Acquired for a research image collection, with no referral diagnosis; a dermoscopy image of a skin lesion; a female patient aged 72: 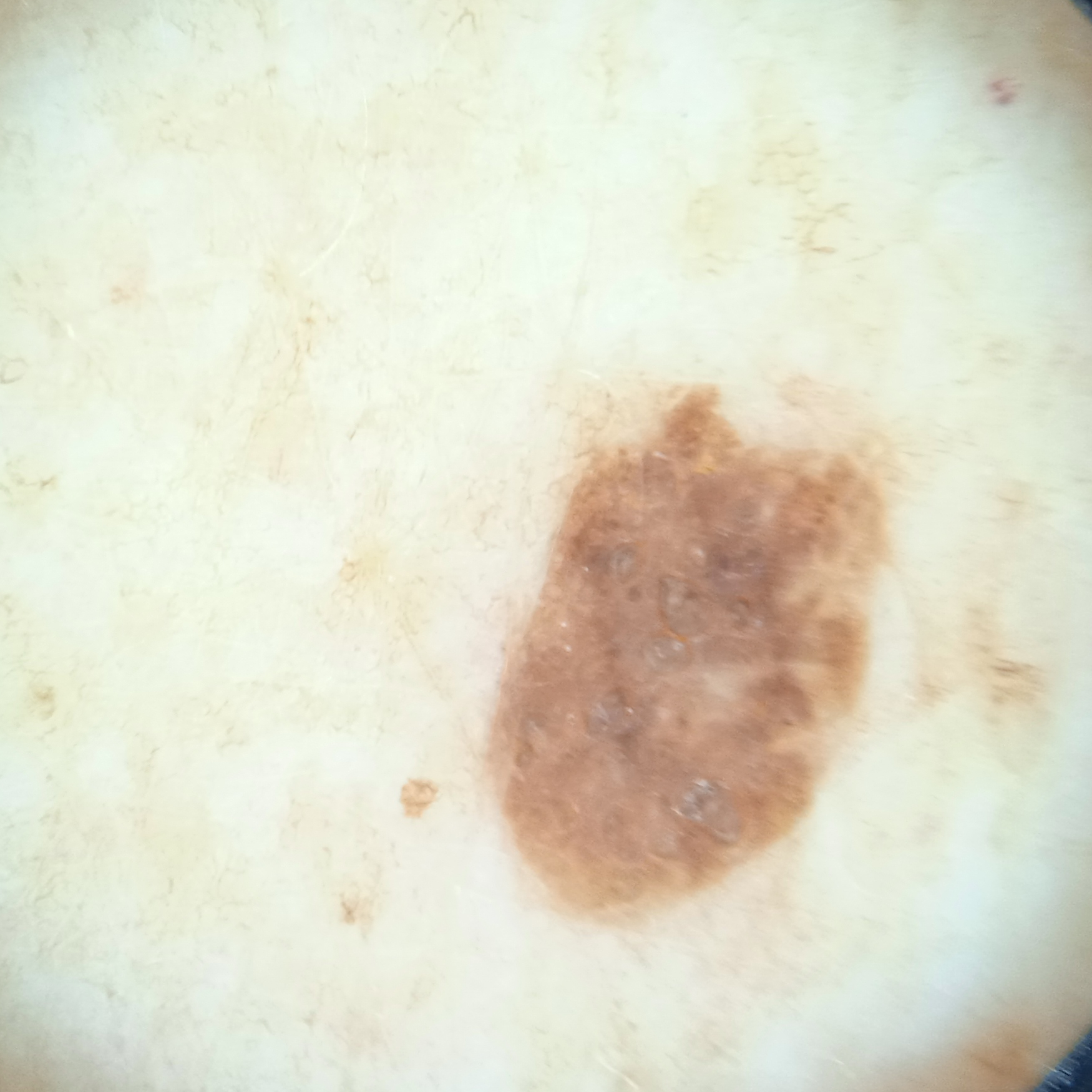Q: Where is the lesion?
A: the back
Q: What was the diagnosis?
A: seborrheic keratosis (dermatologist consensus)